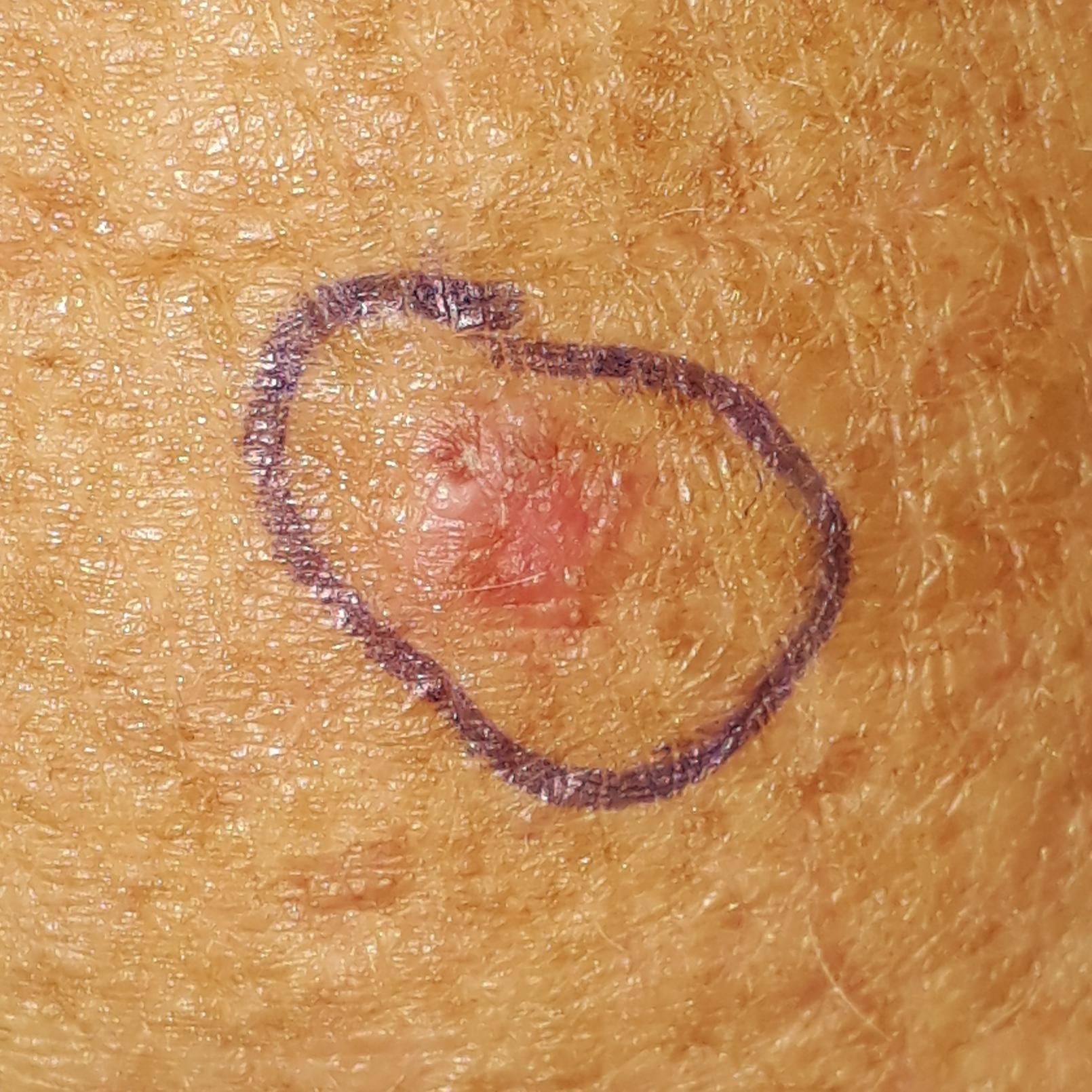The patient is skin type I. A clinical photo of a skin lesion taken with a smartphone. A female subject 70 years of age. The chart notes pesticide exposure, prior skin cancer (patient or family), and prior malignancy (patient or family). The lesion was found on an arm. The lesion measures approximately 6 × 5 mm. The patient describes that the lesion itches. Expert review favored a lesion with uncertain malignant potential — an actinic keratosis.